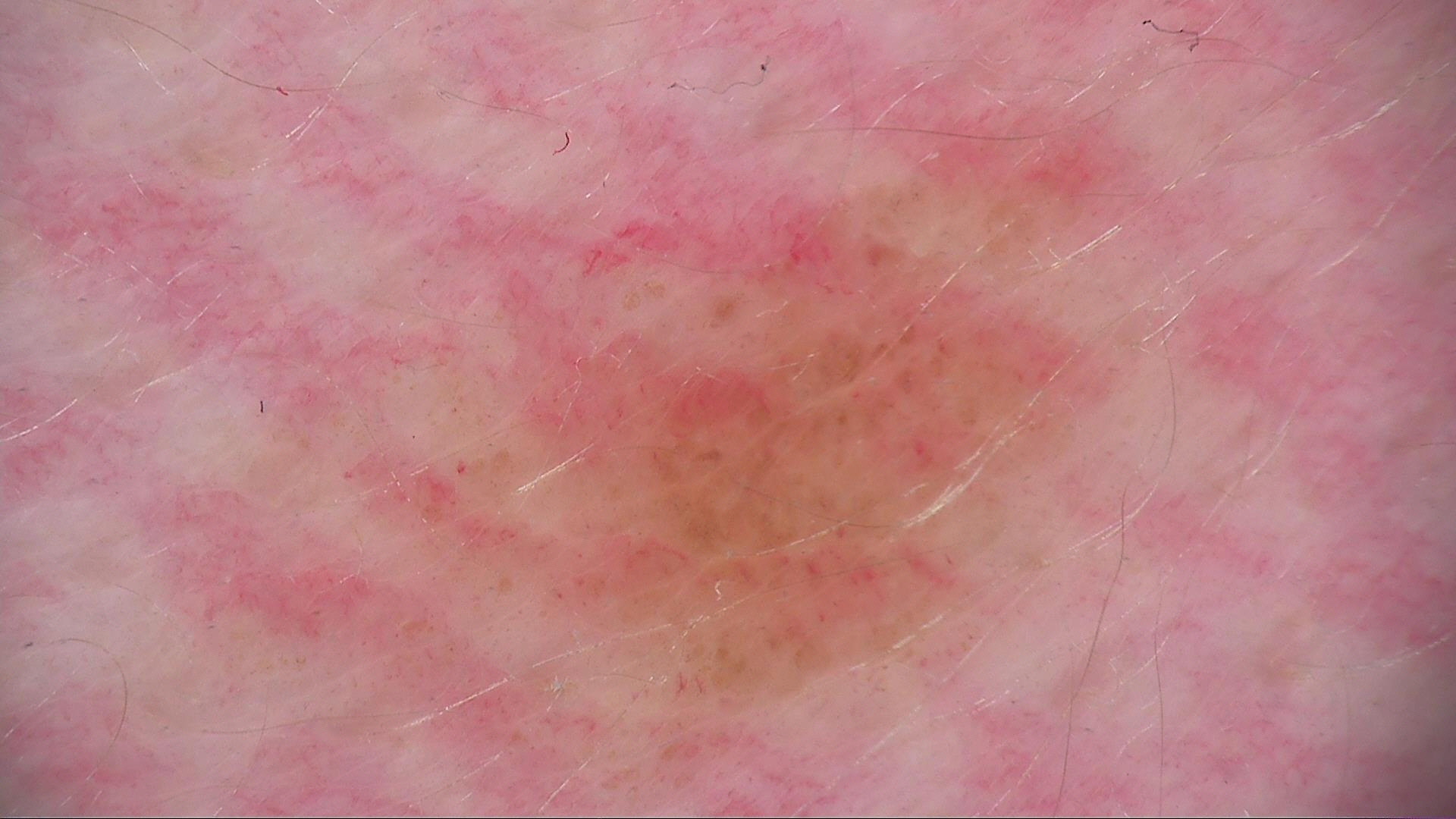assessment: dysplastic junctional nevus (expert consensus).